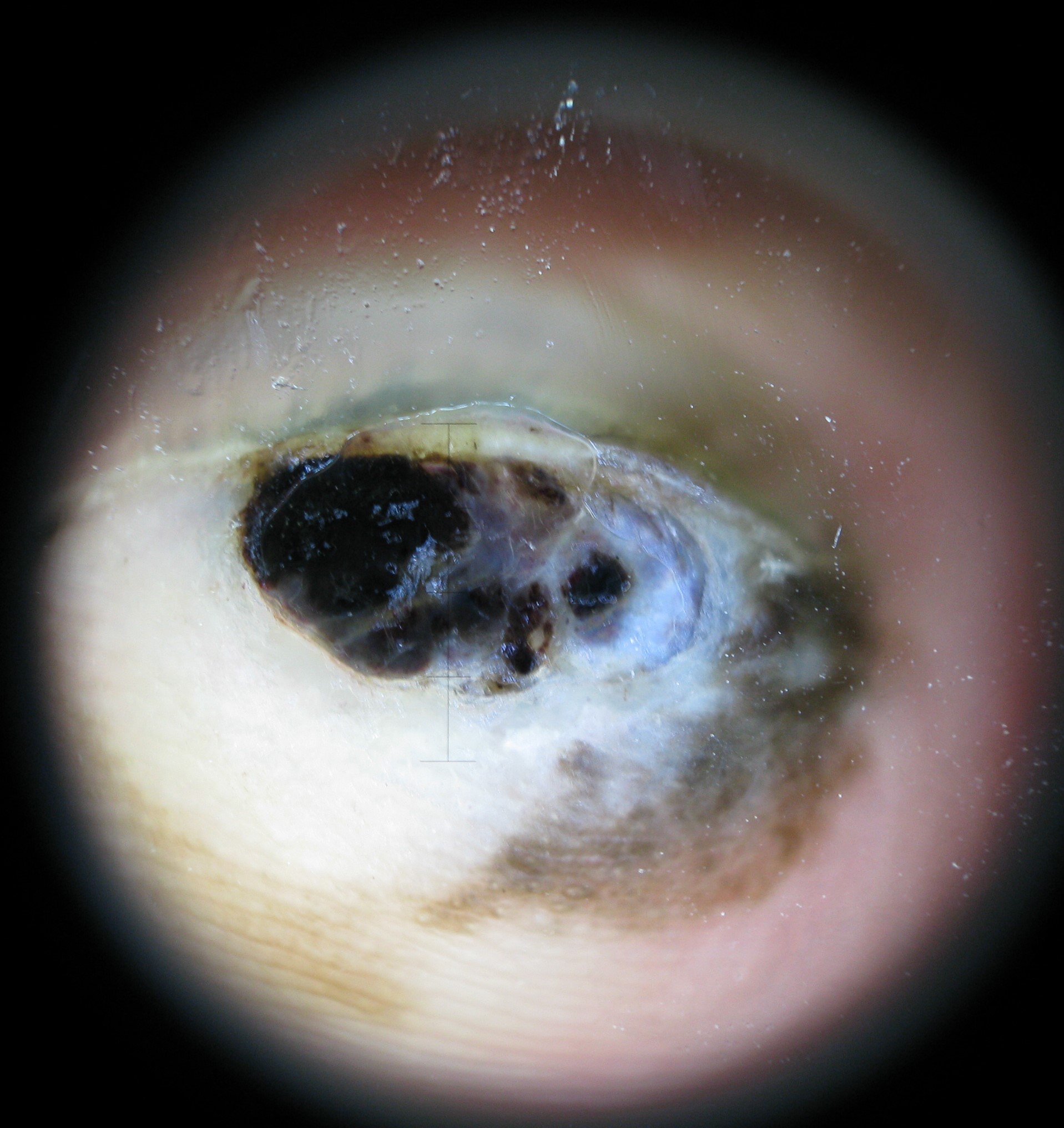Findings:
A dermatoscopic image of a skin lesion.
Conclusion:
The biopsy diagnosis was a skin cancer — an acral nodular melanoma.